A female patient approximately 70 years of age. The patient is Fitzpatrick skin type II. A dermoscopic image of a skin lesion.
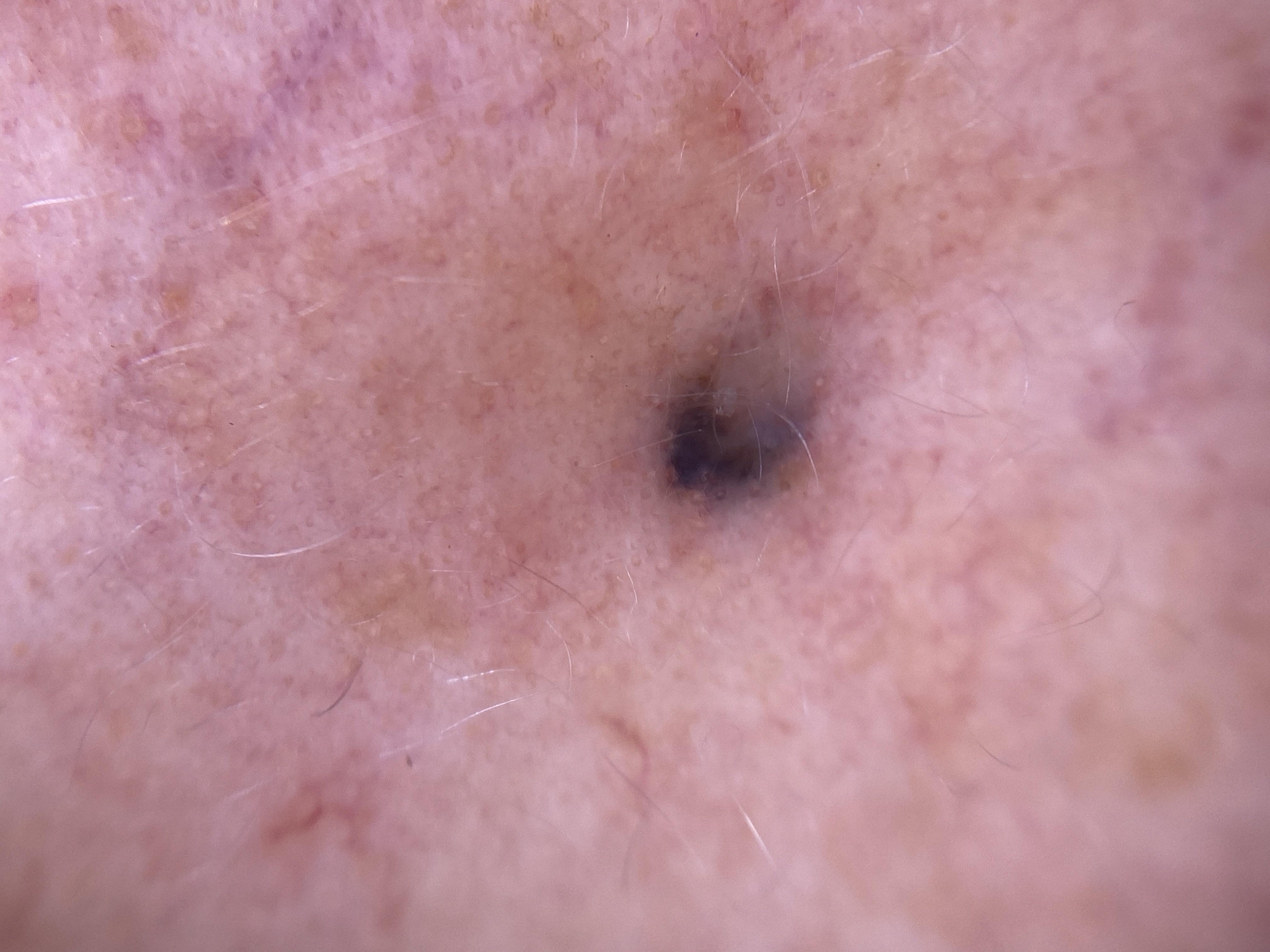Located on the head or neck. The clinical impression was a lesion of melanocytic origin — a nevus.